A dermatoscopic image of a skin lesion:
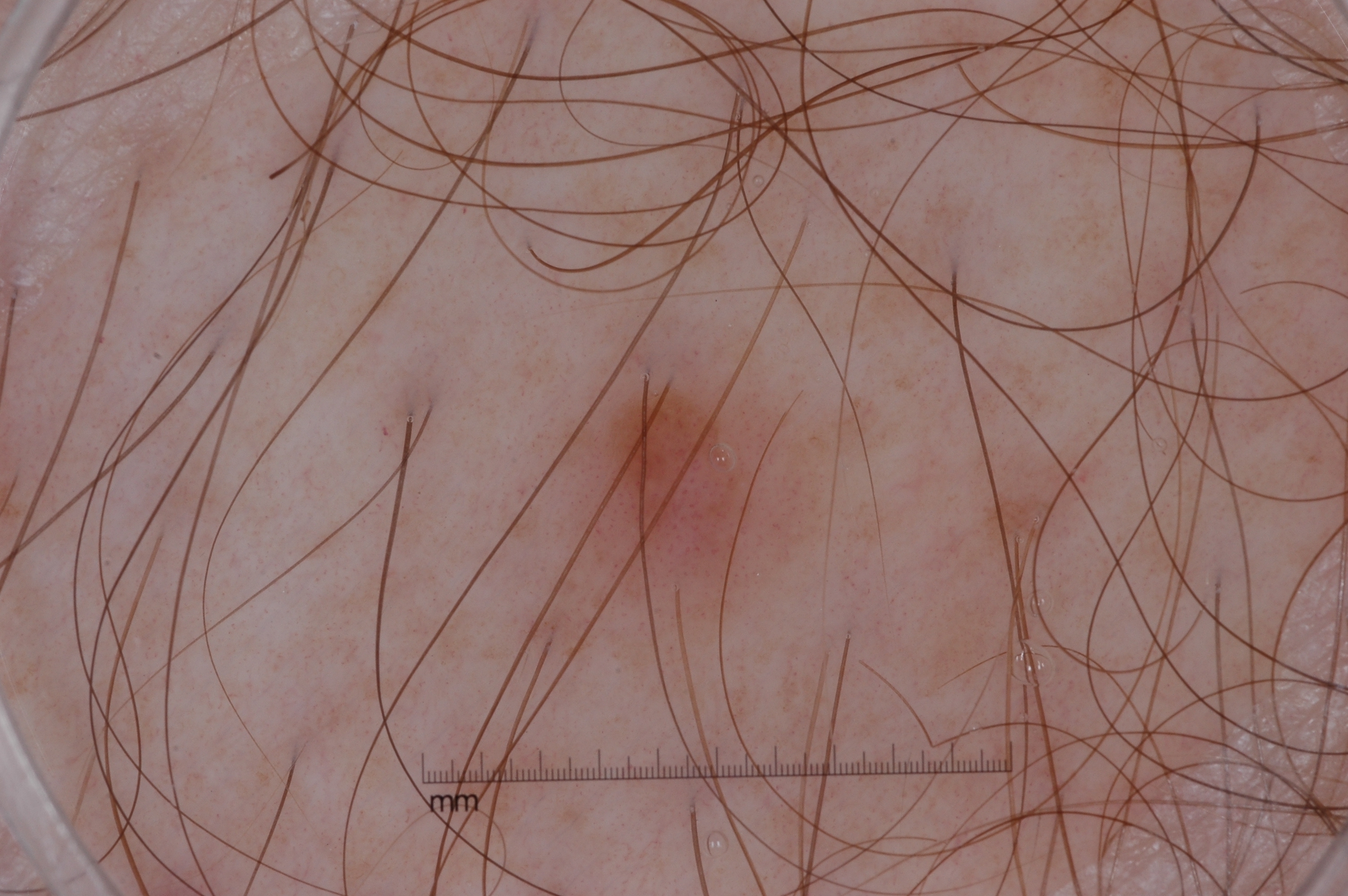With coordinates (x1, y1, x2, y2), the lesion is located at 537, 343, 832, 658. On dermoscopy, the lesion shows no milia-like cysts, negative network, streaks, or pigment network. Clinically diagnosed as a melanocytic nevus, a benign skin lesion.